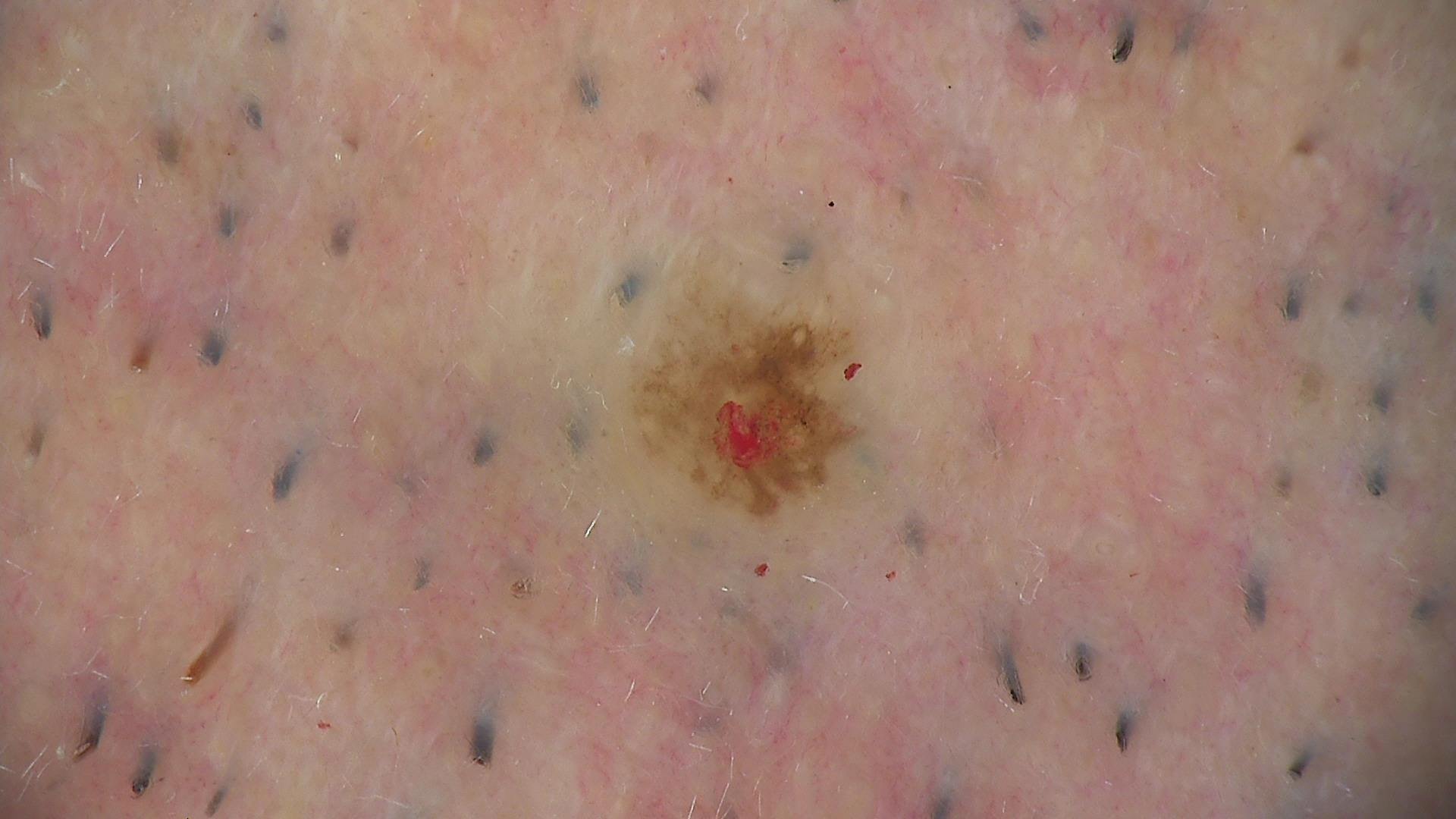  image: dermatoscopy
  lesion_type:
    main_class: banal
    pattern: compound
  diagnosis:
    name: Miescher nevus
    code: mcb
    malignancy: benign
    super_class: melanocytic
    confirmation: expert consensus